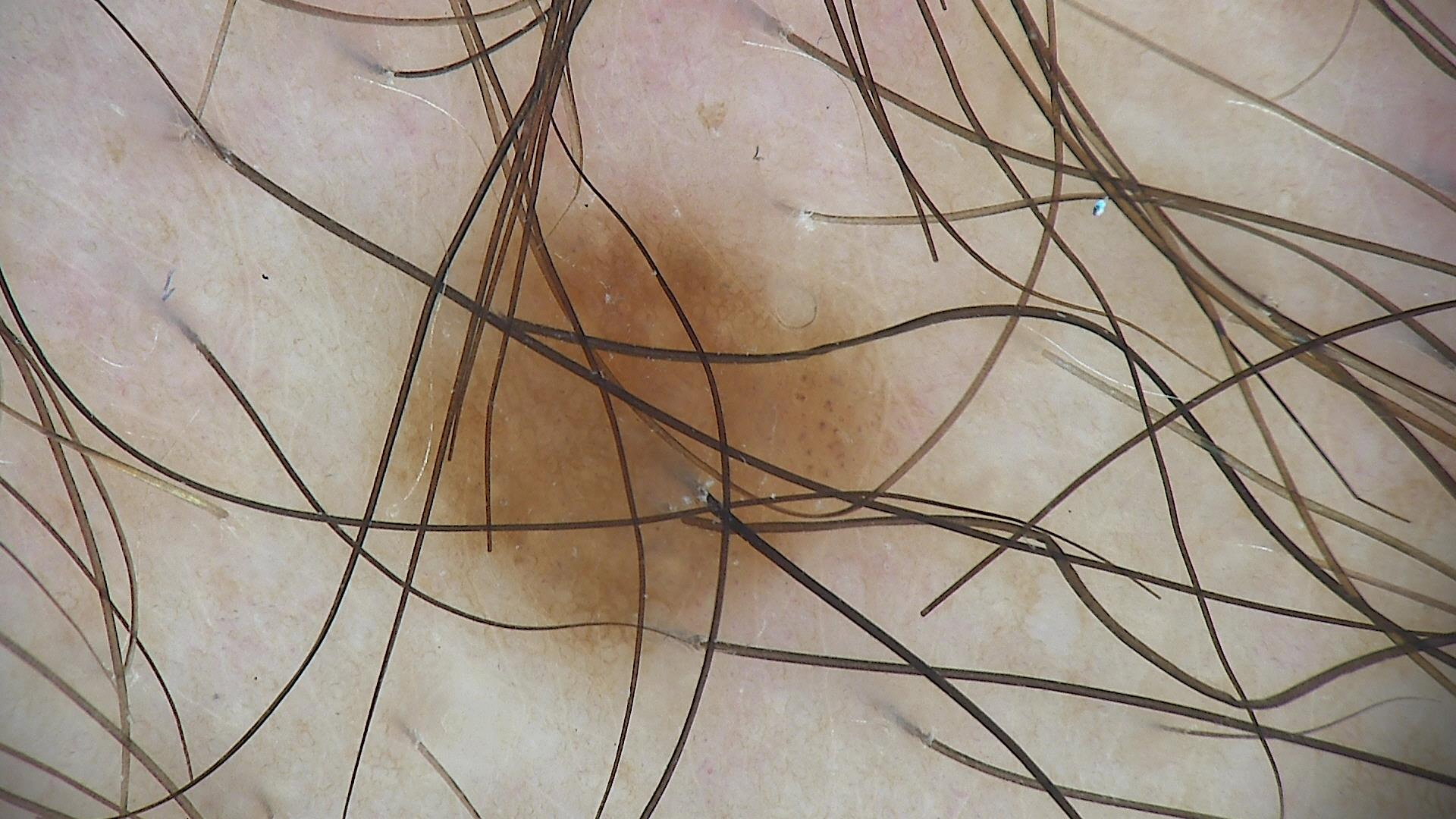Classified as a dysplastic junctional nevus.